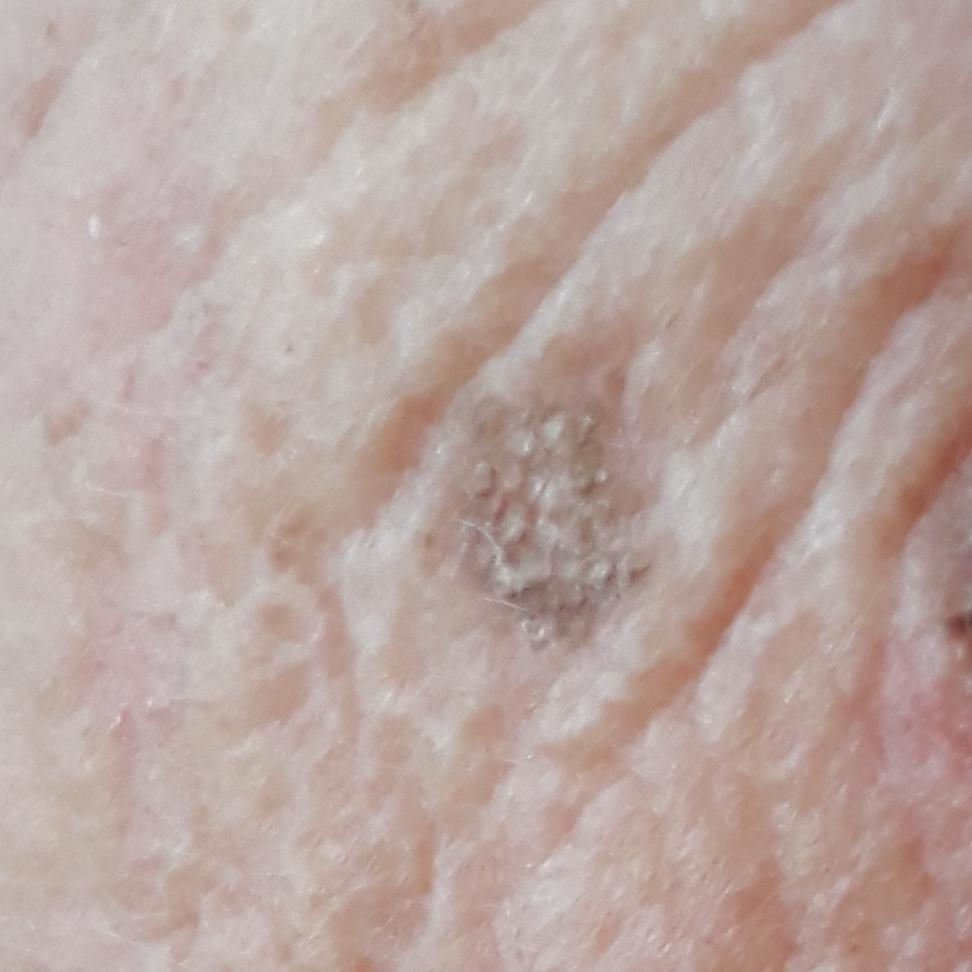<lesion>
<symptoms>
<present>growth, elevation</present>
<absent>itching, pain</absent>
</symptoms>
<diagnosis>
<name>seborrheic keratosis</name>
<code>SEK</code>
<malignancy>benign</malignancy>
<confirmation>clinical consensus</confirmation>
</diagnosis>
</lesion>